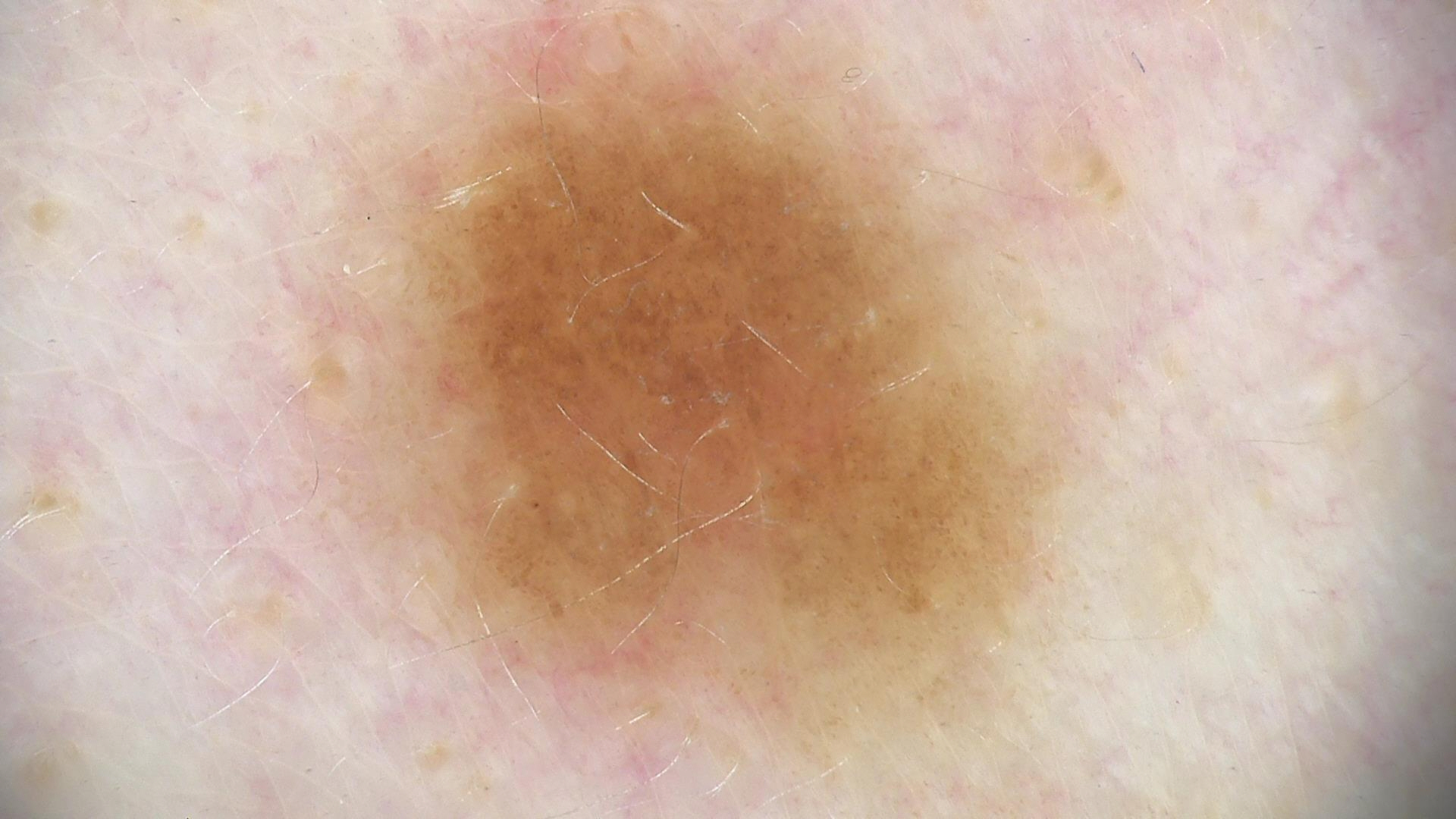Findings:
• class · dysplastic junctional nevus (expert consensus)